The photo was captured at an angle — 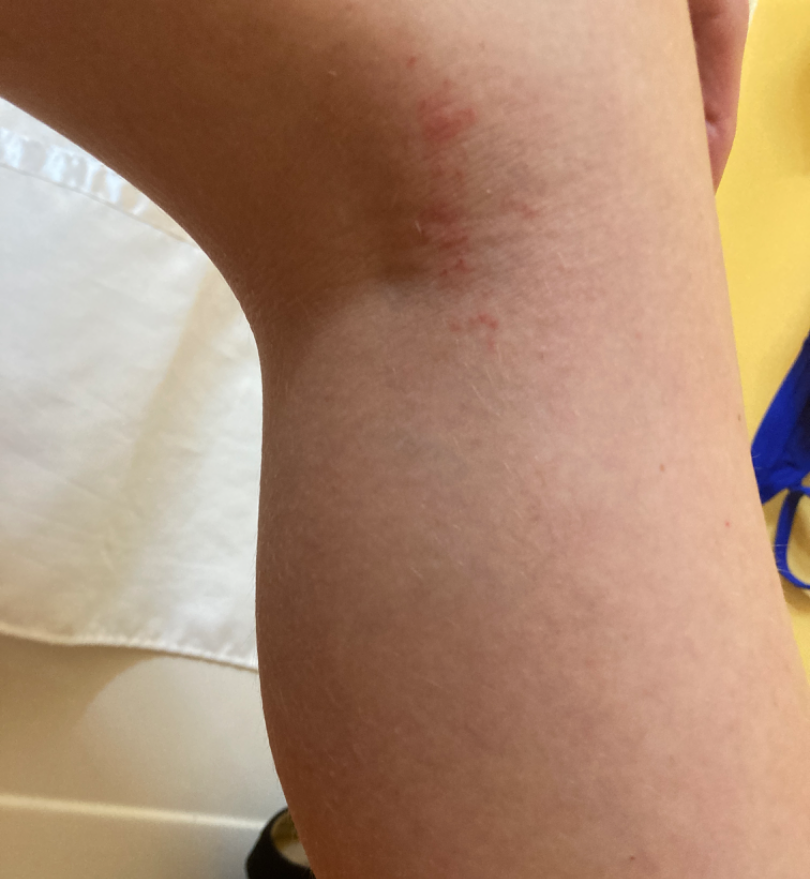Q: Fitzpatrick or Monk tone?
A: Fitzpatrick II
Q: What is the differential diagnosis?
A: Eczema (possible); Allergic Contact Dermatitis (possible)